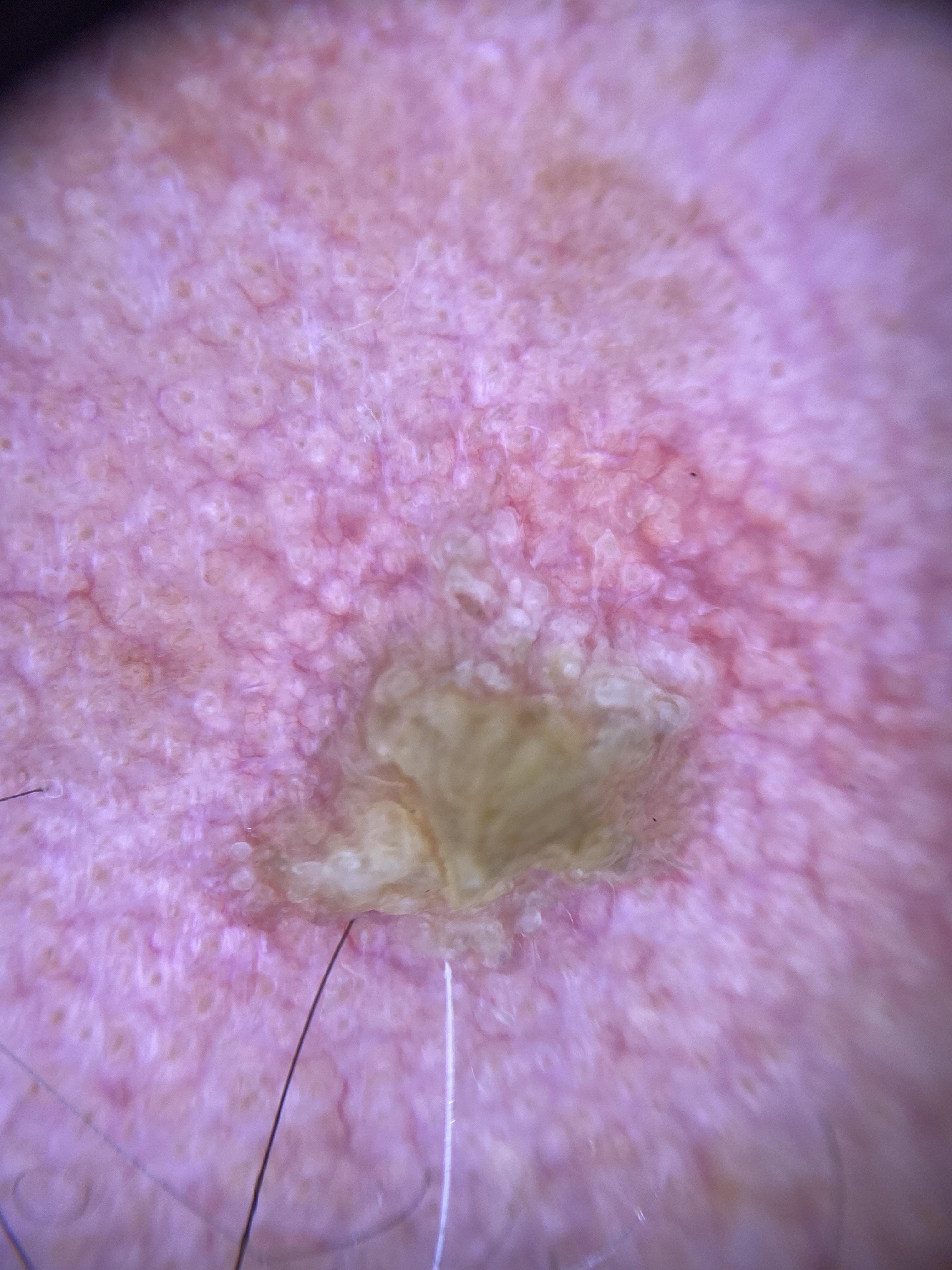{
  "lesion_location": {
    "region": "the head or neck"
  },
  "diagnosis": {
    "name": "Squamous cell carcinoma",
    "malignancy": "malignant",
    "confirmation": "histopathology",
    "lineage": "epidermal"
  }
}